A dermoscopic image of a skin lesion: 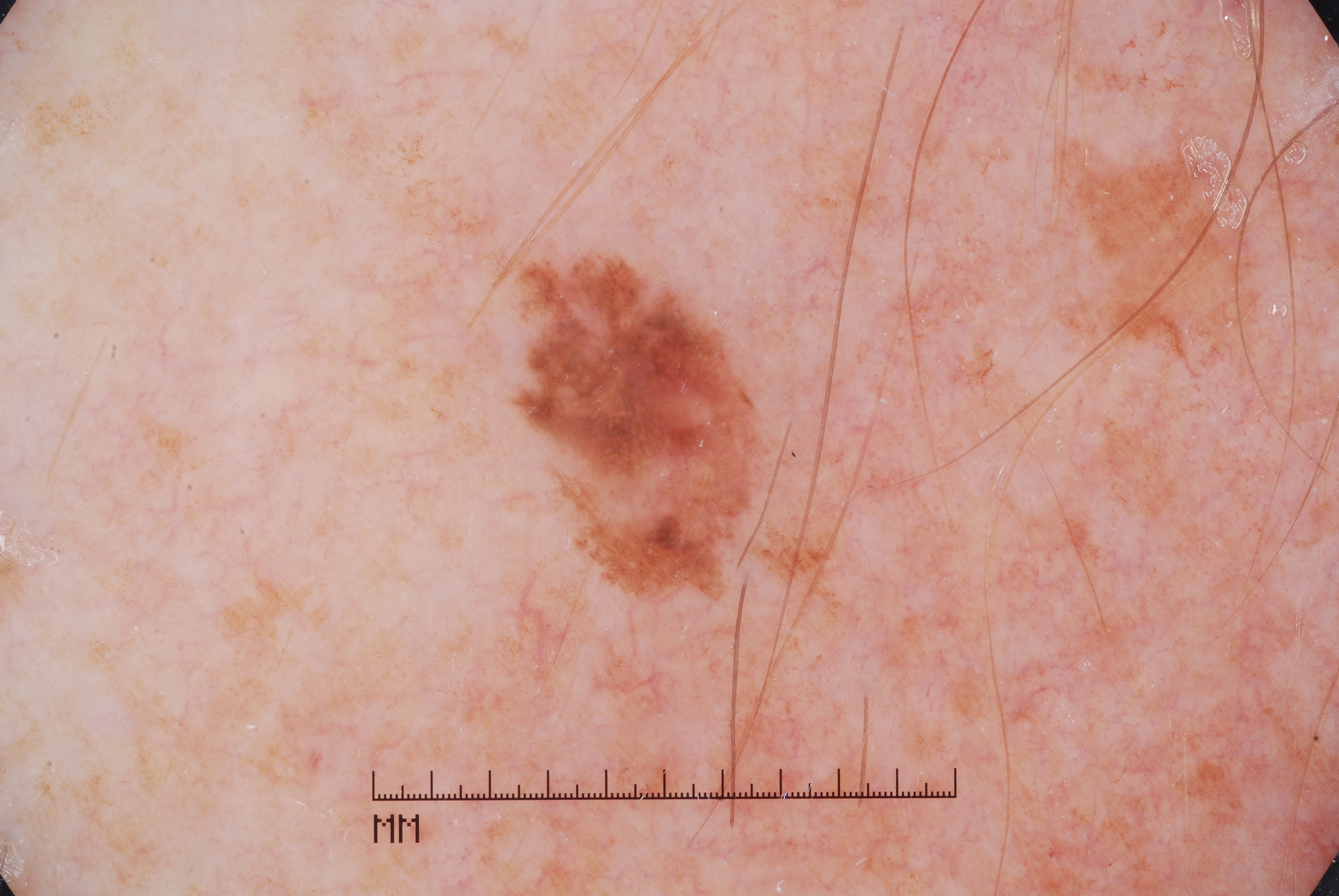lesion size=small | features=milia-like cysts and pigment network; absent: negative network and streaks | bounding box=<box>523, 259, 764, 588</box> | diagnostic label=a melanoma.